Collected as part of a research study, without a referral diagnosis; a male subject age 79; the patient describes having few moles overall; a clinical photograph of a skin lesion — 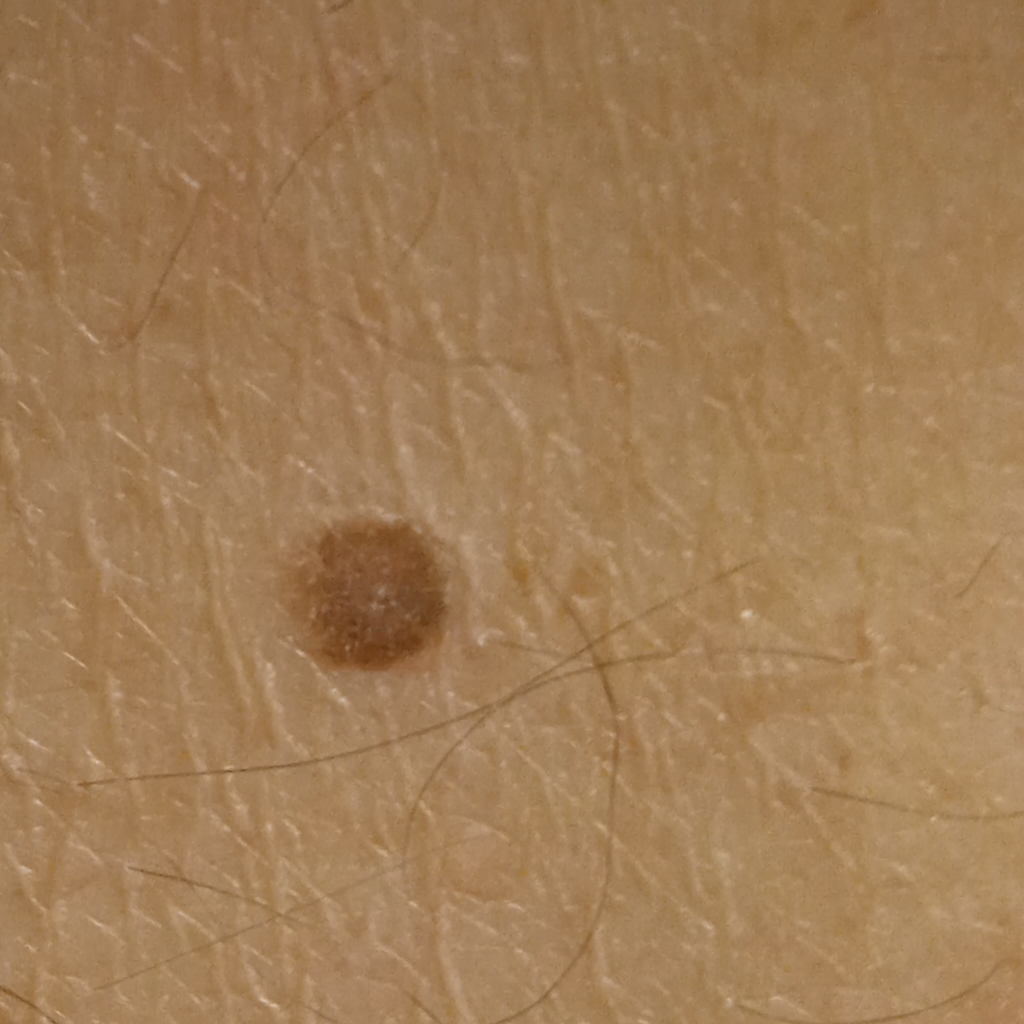Q: How large is the lesion?
A: 5.8 mm
Q: What was the diagnosis?
A: melanocytic nevus (dermatologist consensus)